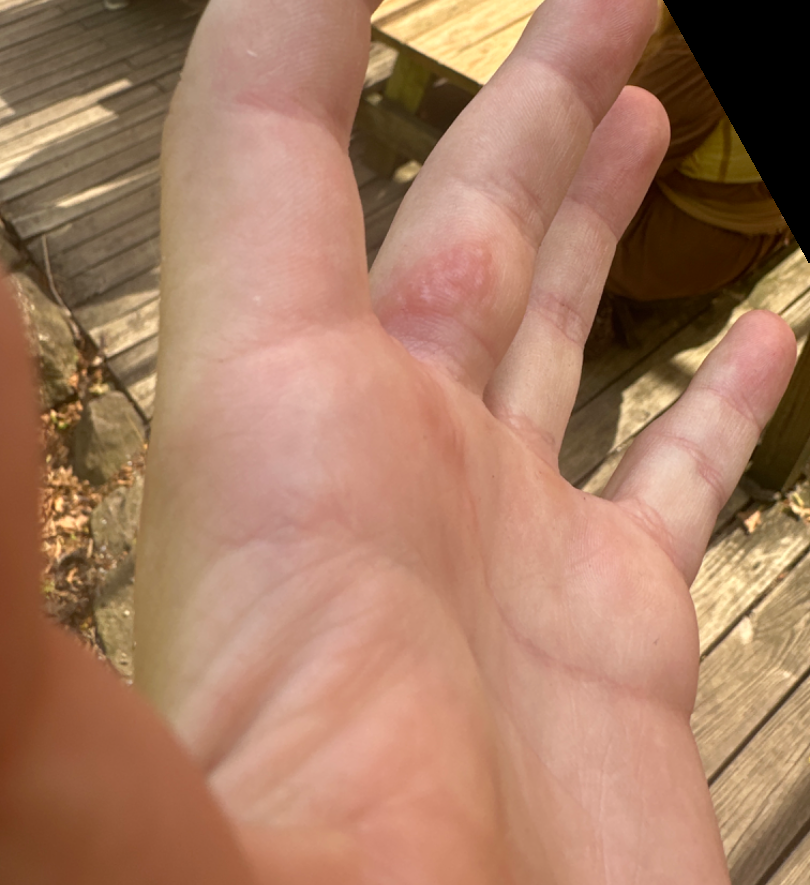Texture is reported as raised or bumpy. The photo was captured at an angle. No constitutional symptoms were reported. The contributor reports pain, itching and burning. Located on the arm and palm. Most consistent with Herpes Simplex; also on the differential is Allergic Contact Dermatitis; also raised was Eczema.